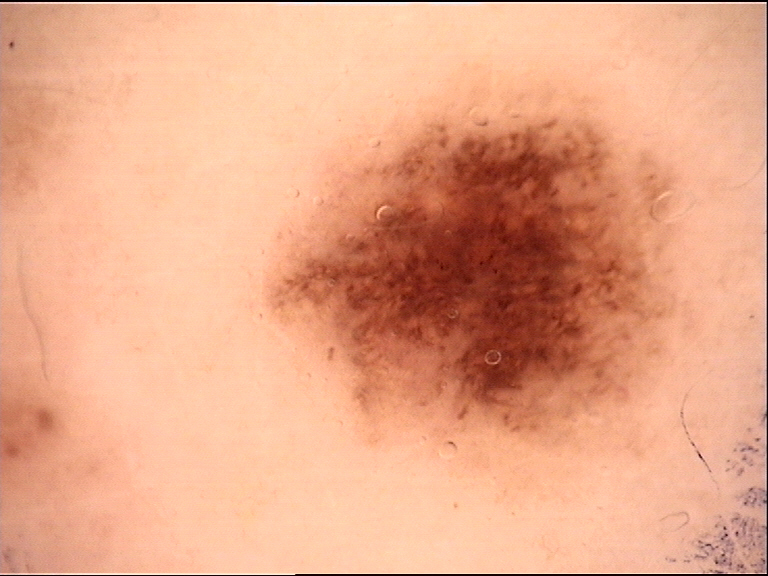A dermatoscopic image of a skin lesion.
Classified as a dysplastic junctional nevus.